The patient says their skin tans without first burning · acquired for a research image collection, with no referral diagnosis · the patient reports a personal history of cancer and a family history of skin cancer — 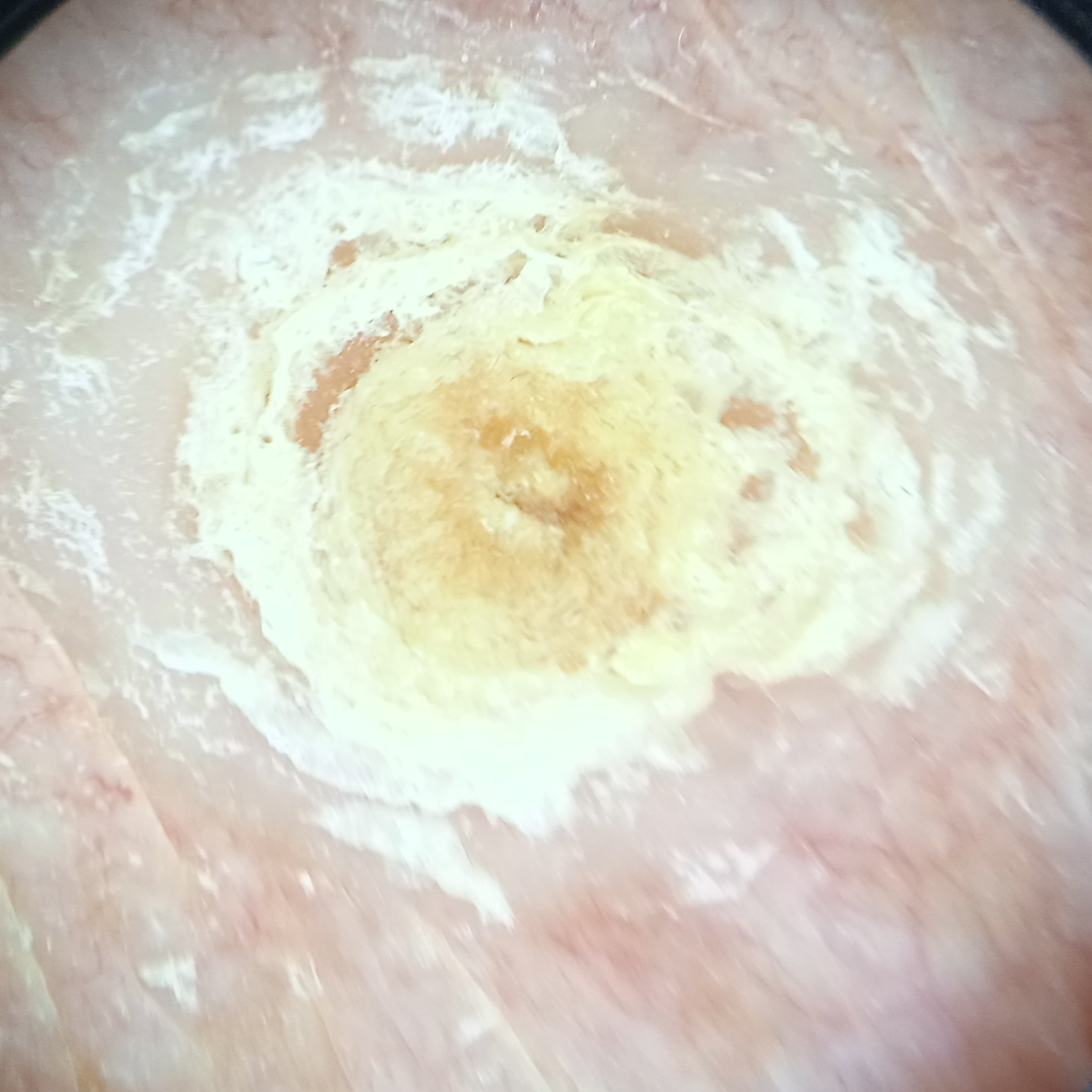Clinical context: Measuring roughly 12.5 mm. Impression: The dermatologists' assessment was a squamous cell carcinoma.